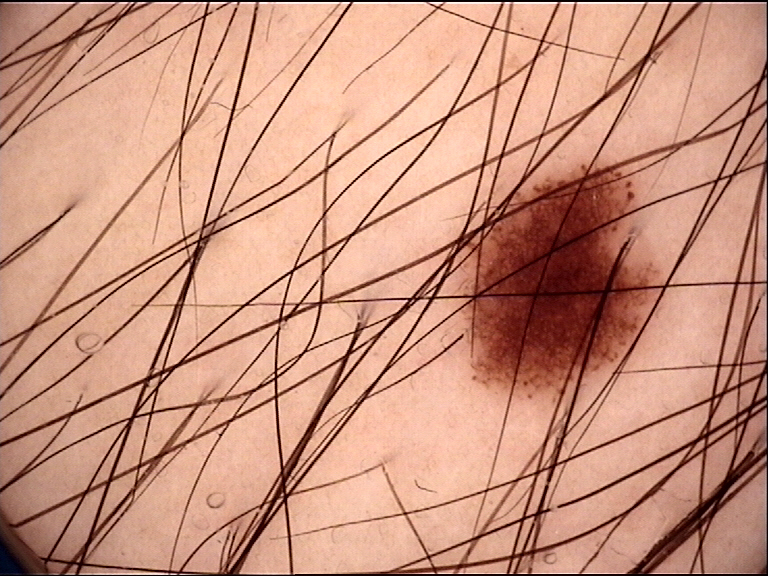The diagnosis was a dysplastic junctional nevus.